A dermoscopic photograph of a skin lesion:
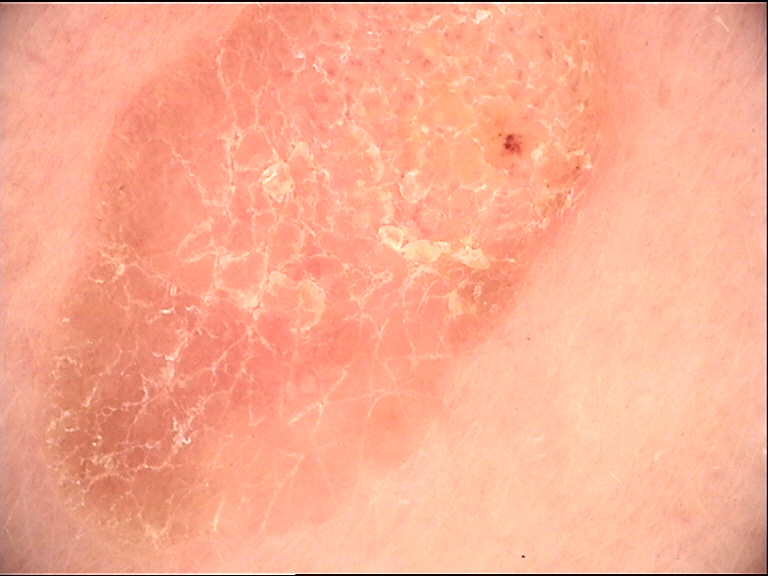{"lesion_type": {"main_class": "keratinocytic"}, "diagnosis": {"name": "seborrheic keratosis", "code": "sk", "malignancy": "benign", "super_class": "non-melanocytic", "confirmation": "expert consensus"}}